This image was taken at an angle. The affected area is the arm. The patient is 30–39, male: 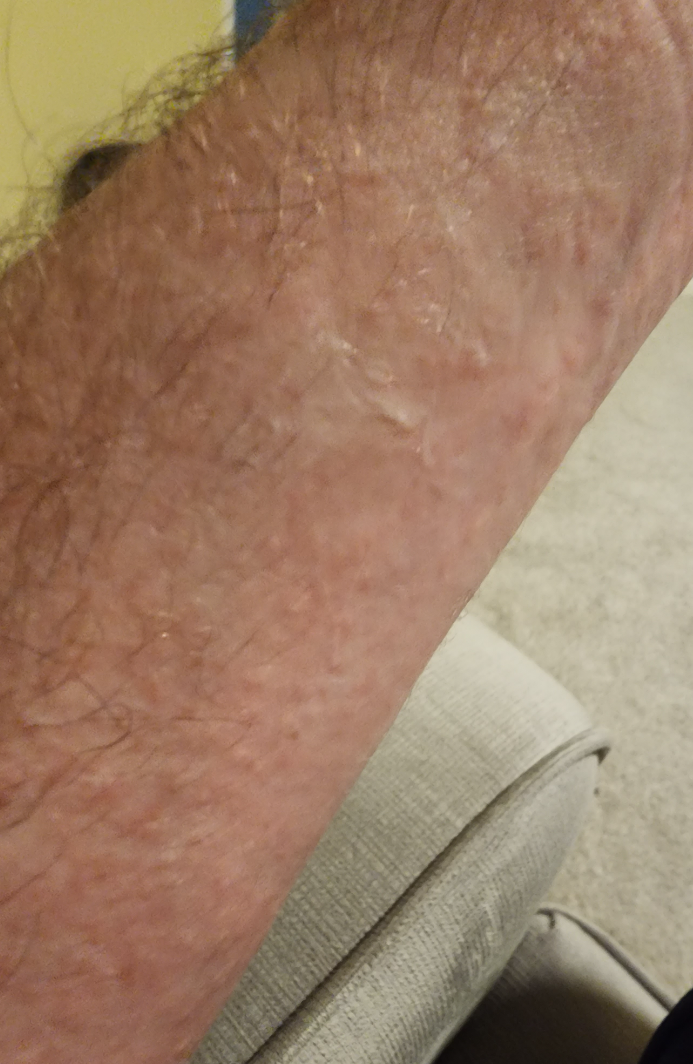<summary>
  <texture>raised or bumpy</texture>
  <systemic_symptoms>none reported</systemic_symptoms>
  <symptoms>itching, bothersome appearance</symptoms>
  <duration>about one day</duration>
  <patient_category>a rash</patient_category>
  <differential>
    <leading>Eczema</leading>
    <considered>Allergic Contact Dermatitis</considered>
    <unlikely>Viral Exanthem, Drug Rash</unlikely>
  </differential>
</summary>